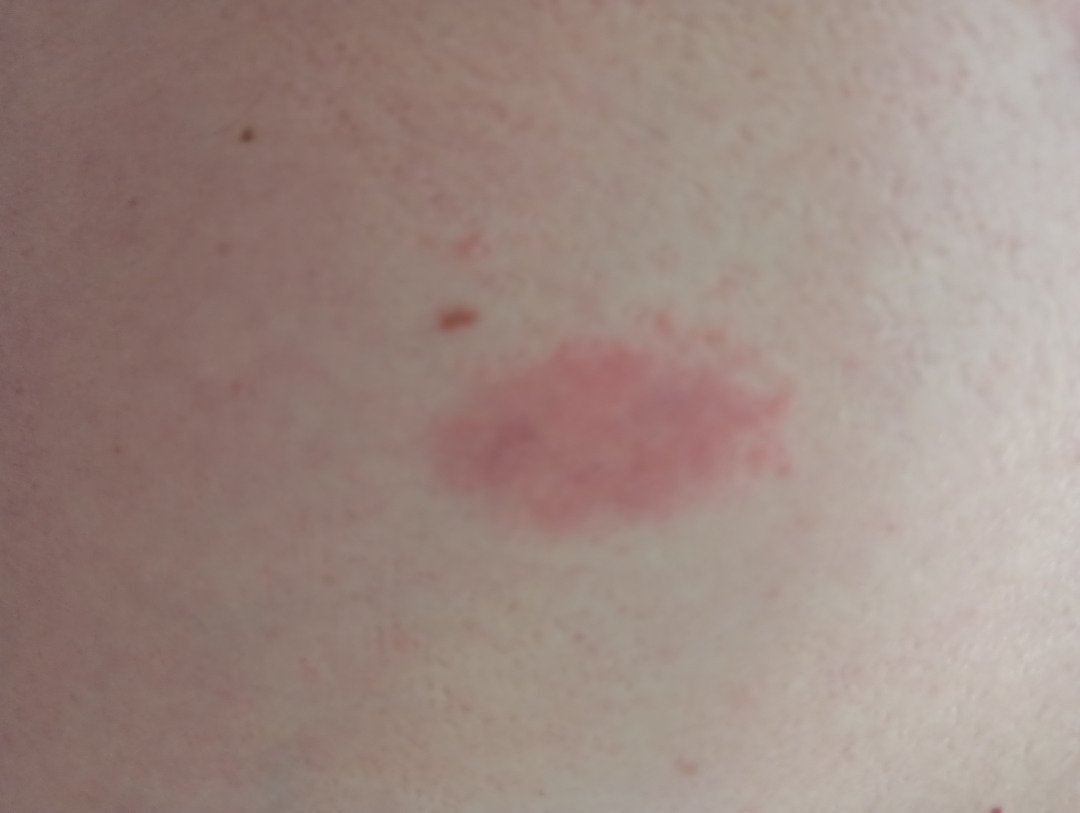Assessment: The skin condition could not be confidently assessed from this image.